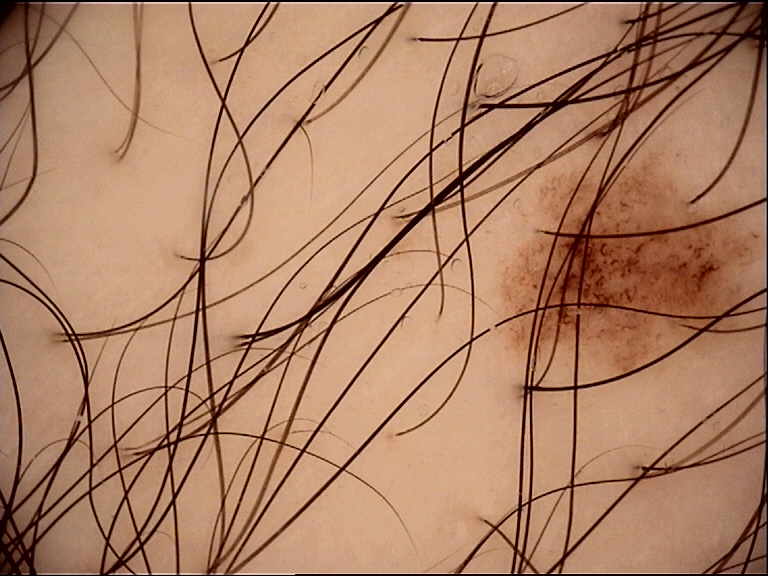Q: What was the diagnostic impression?
A: dysplastic junctional nevus (expert consensus)